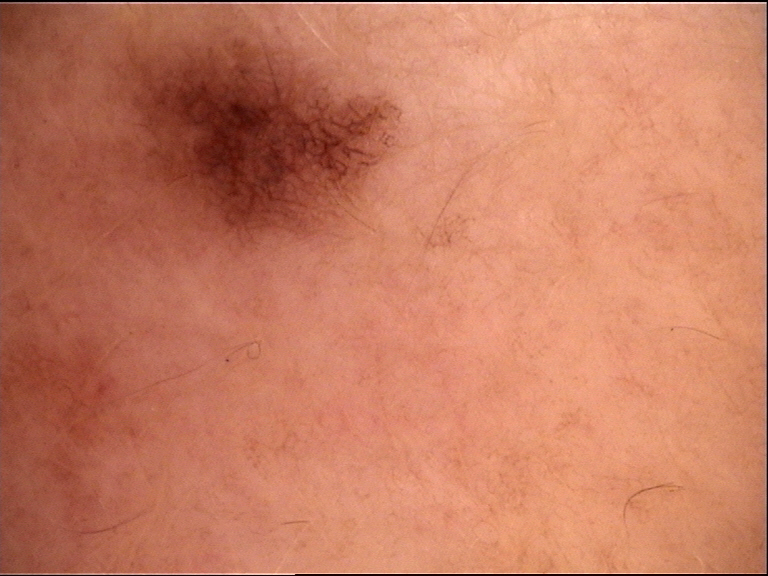image: dermoscopy
diagnosis:
  name: dysplastic junctional nevus
  code: jd
  malignancy: benign
  super_class: melanocytic
  confirmation: expert consensus